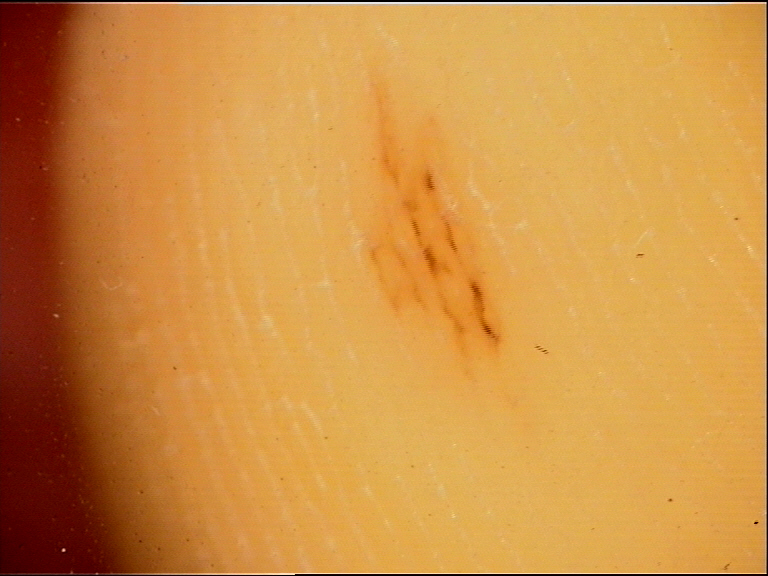assessment: acral junctional nevus (expert consensus).